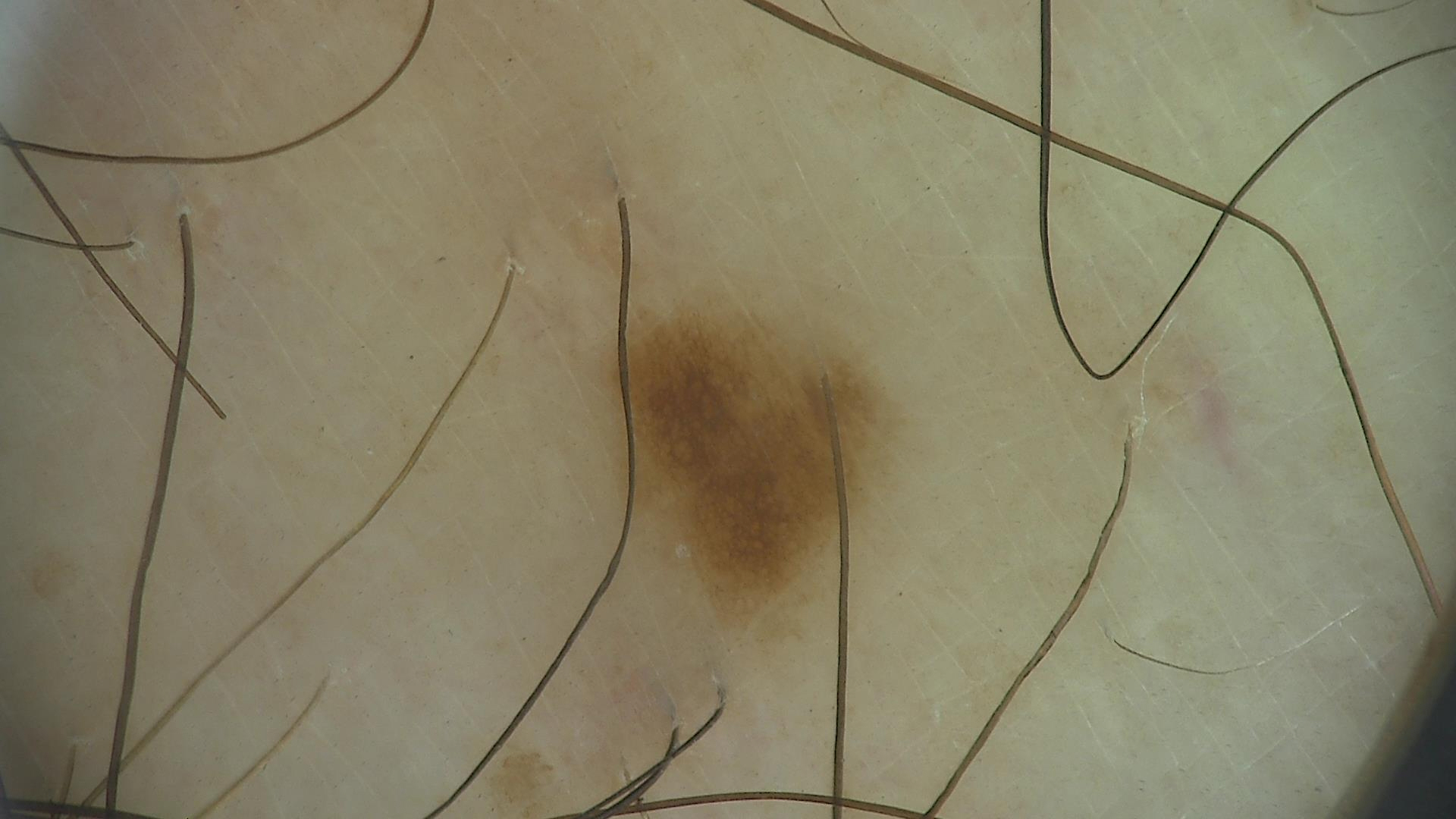assessment = junctional nevus (expert consensus)